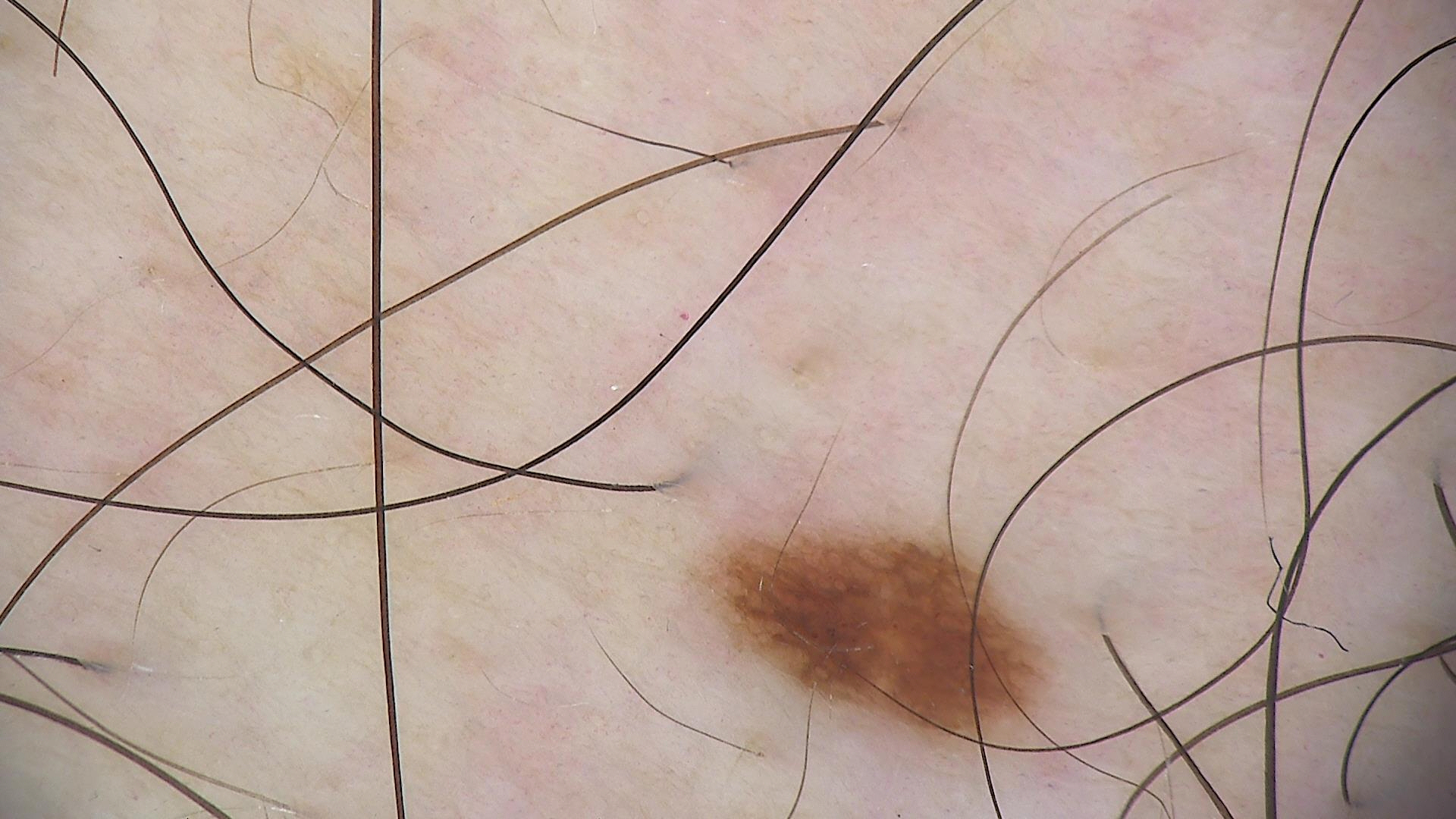Dermoscopy of a skin lesion. Labeled as a dysplastic junctional nevus.